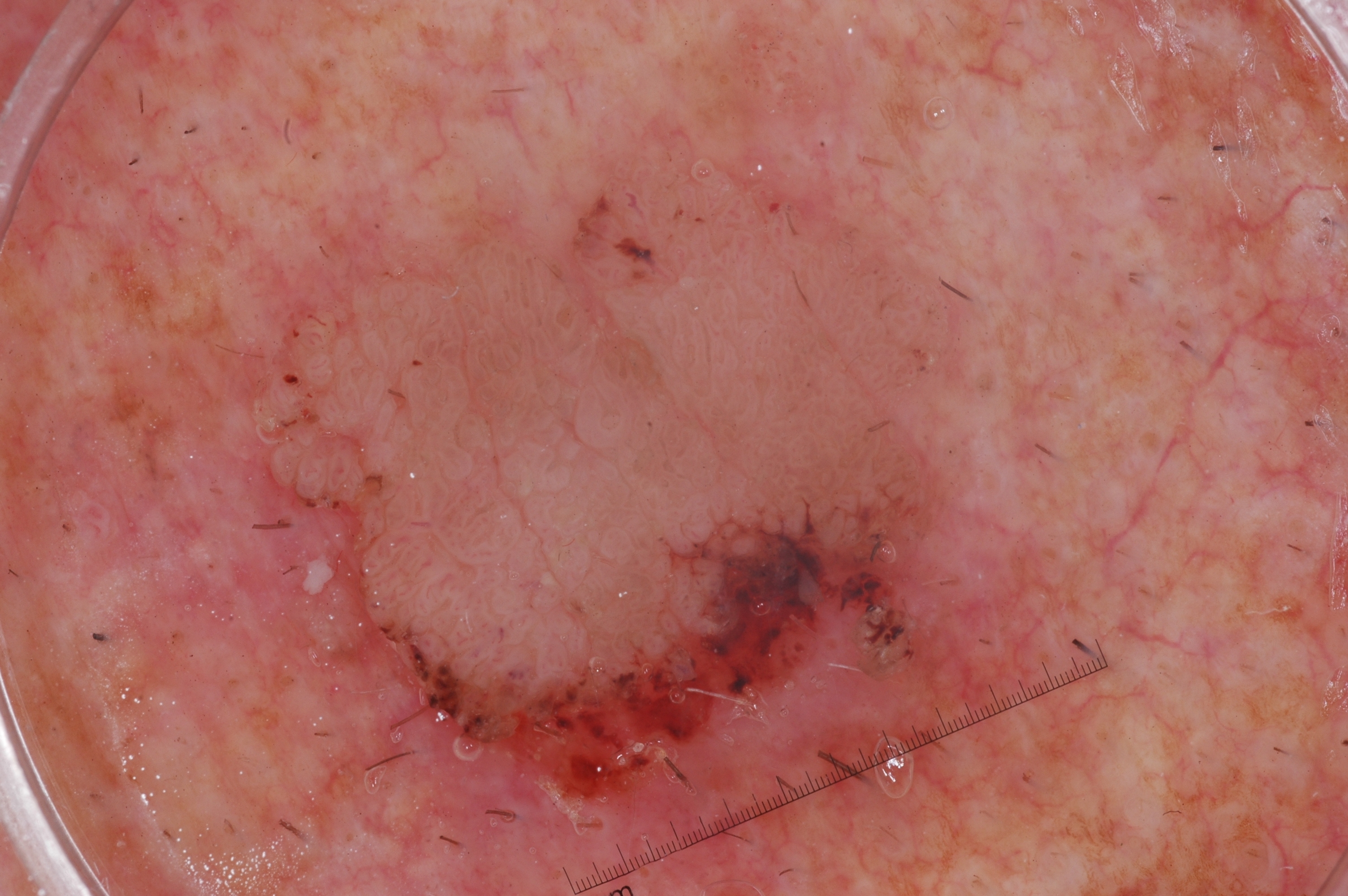A male subject, approximately 70 years of age.
A dermoscopic image of a skin lesion.
A large lesion occupying much of the field.
The lesion is bounded by x1=248, y1=96, x2=1059, y2=802.
On dermoscopy, the lesion shows no pigment network, negative network, streaks, or milia-like cysts.
Diagnosed as a seborrheic keratosis, a benign lesion.